A dermoscopic photograph of a skin lesion.
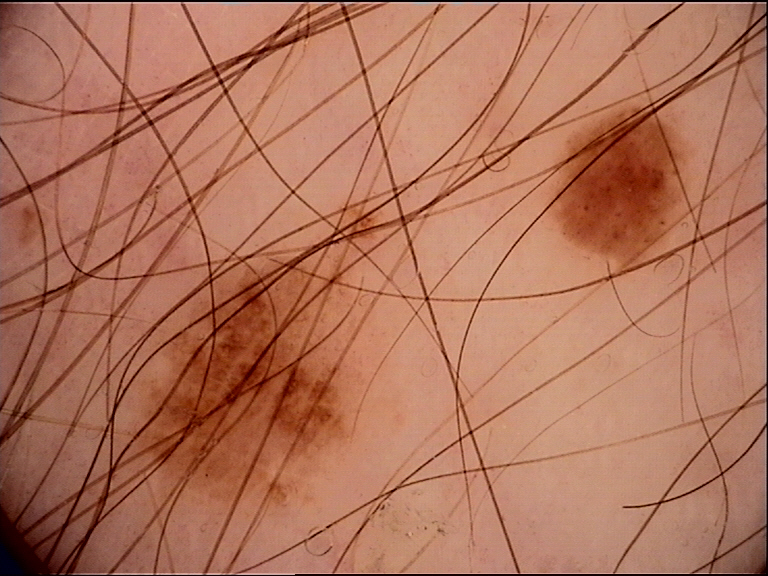The diagnosis was a benign lesion — a dysplastic junctional nevus.